Reported lesion symptoms include itching. The lesion involves the top or side of the foot. The patient indicates the condition has been present for more than one year. Texture is reported as raised or bumpy. An image taken at an angle — 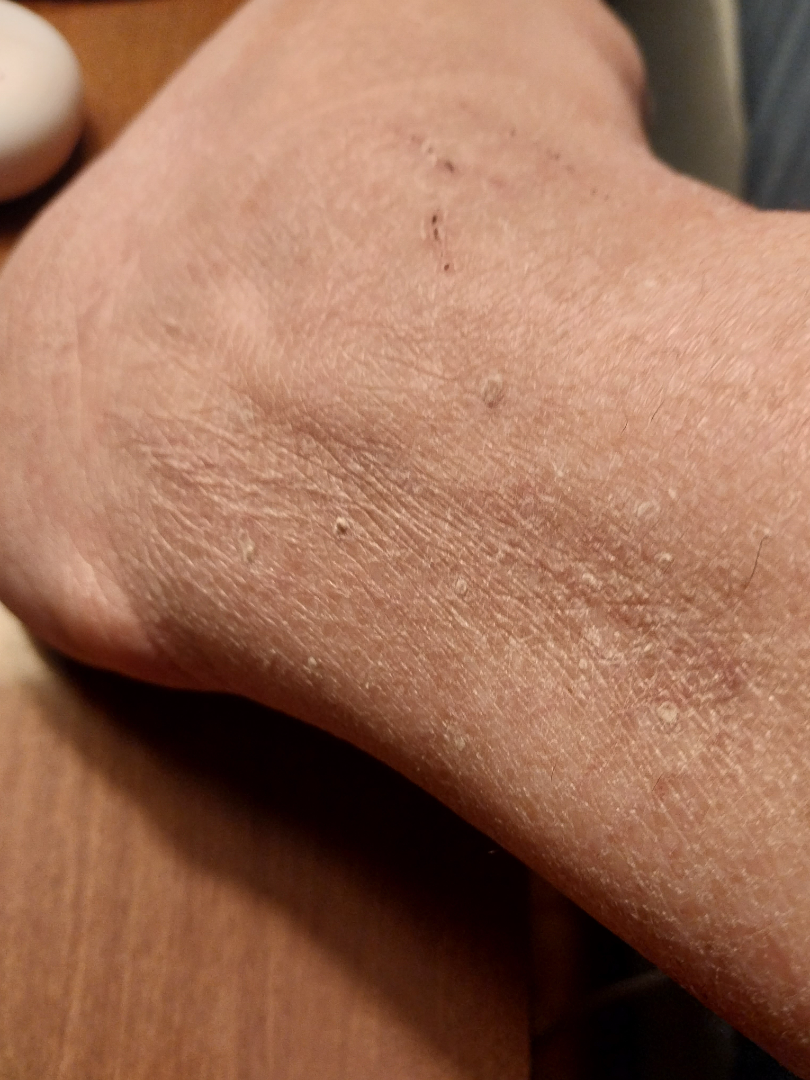{"differential": "Eczema"}